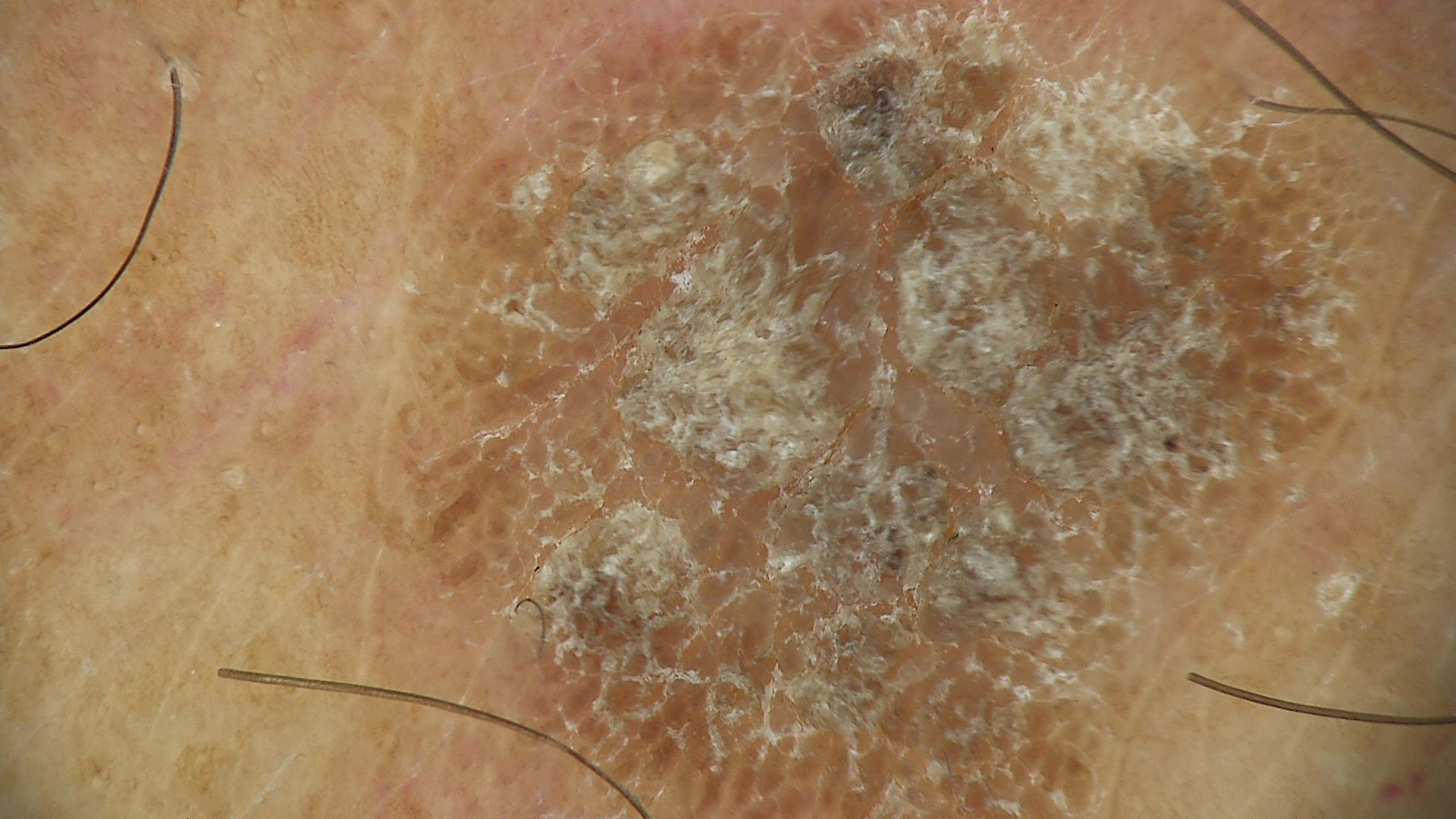modality: dermoscopy | subtype: keratinocytic | diagnostic label: seborrheic keratosis (expert consensus).